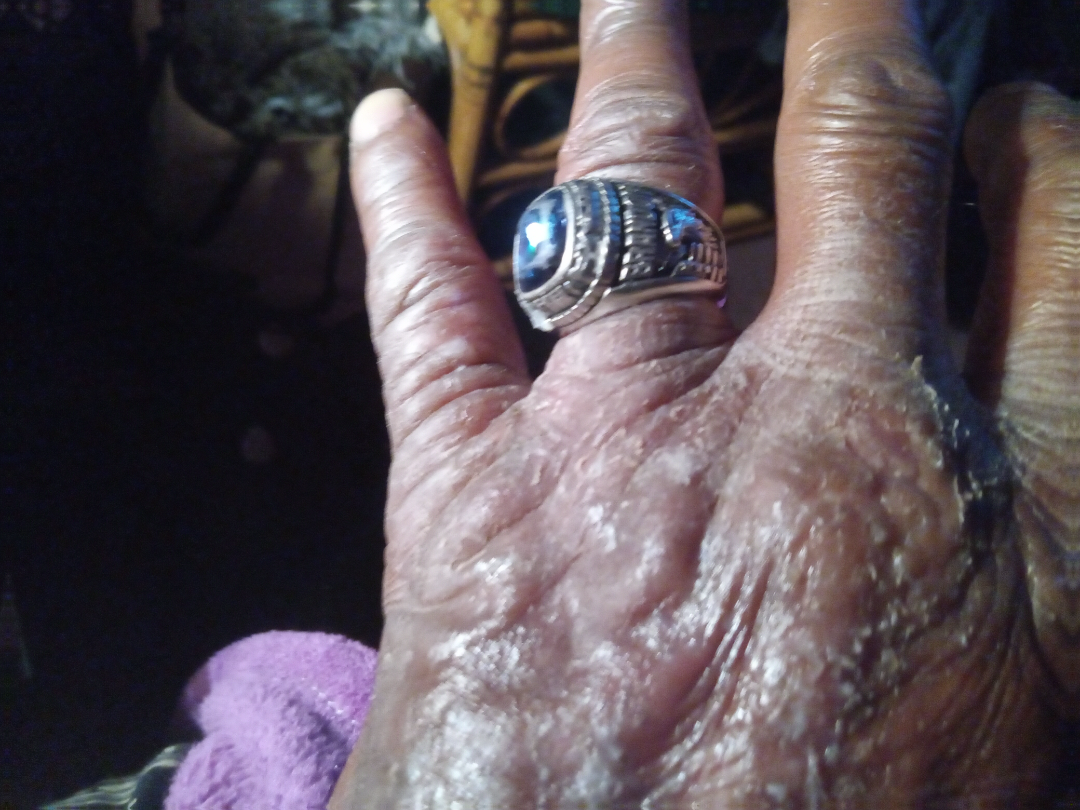assessment — no findings on review